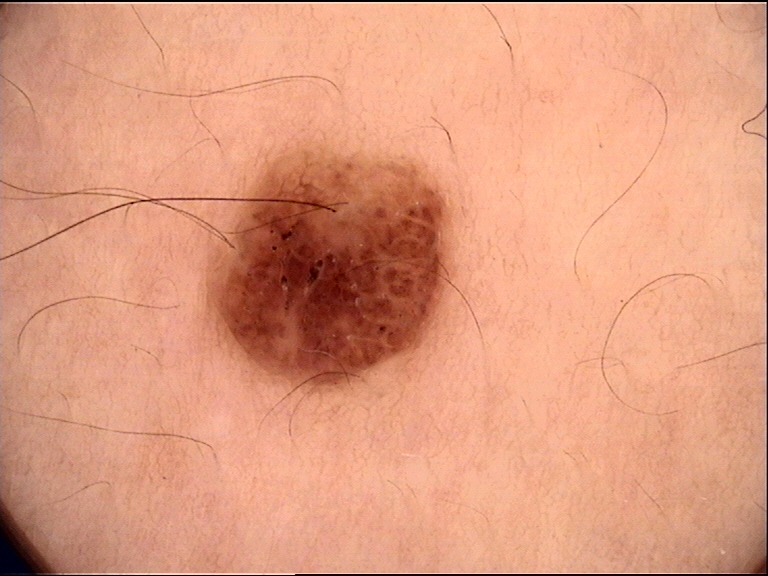Case:
* category · banal
* diagnosis · compound nevus (expert consensus)